Recorded as Fitzpatrick skin type I. History notes pesticide exposure, no prior skin cancer (patient or family), and no alcohol use. A clinical close-up photograph of a skin lesion. A female subject 74 years of age:
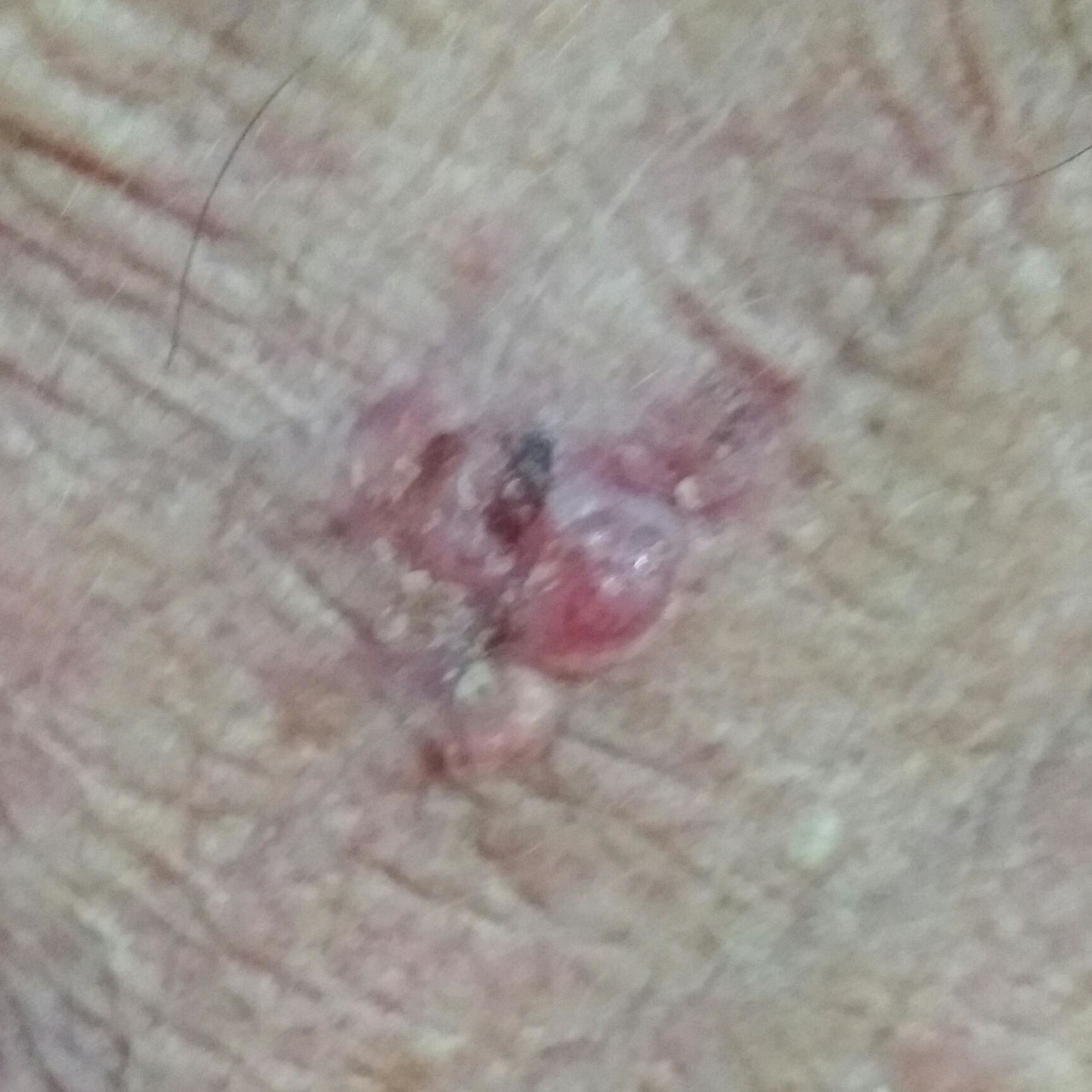<lesion>
<lesion_location>the face</lesion_location>
<lesion_size>
<diameter_1_mm>15.0</diameter_1_mm>
<diameter_2_mm>10.0</diameter_2_mm>
</lesion_size>
<symptoms>
<present>bleeding, growth, pain, itching, elevation</present>
<absent>change in appearance</absent>
</symptoms>
<diagnosis>
<name>basal cell carcinoma</name>
<code>BCC</code>
<malignancy>malignant</malignancy>
<confirmation>histopathology</confirmation>
</diagnosis>
</lesion>